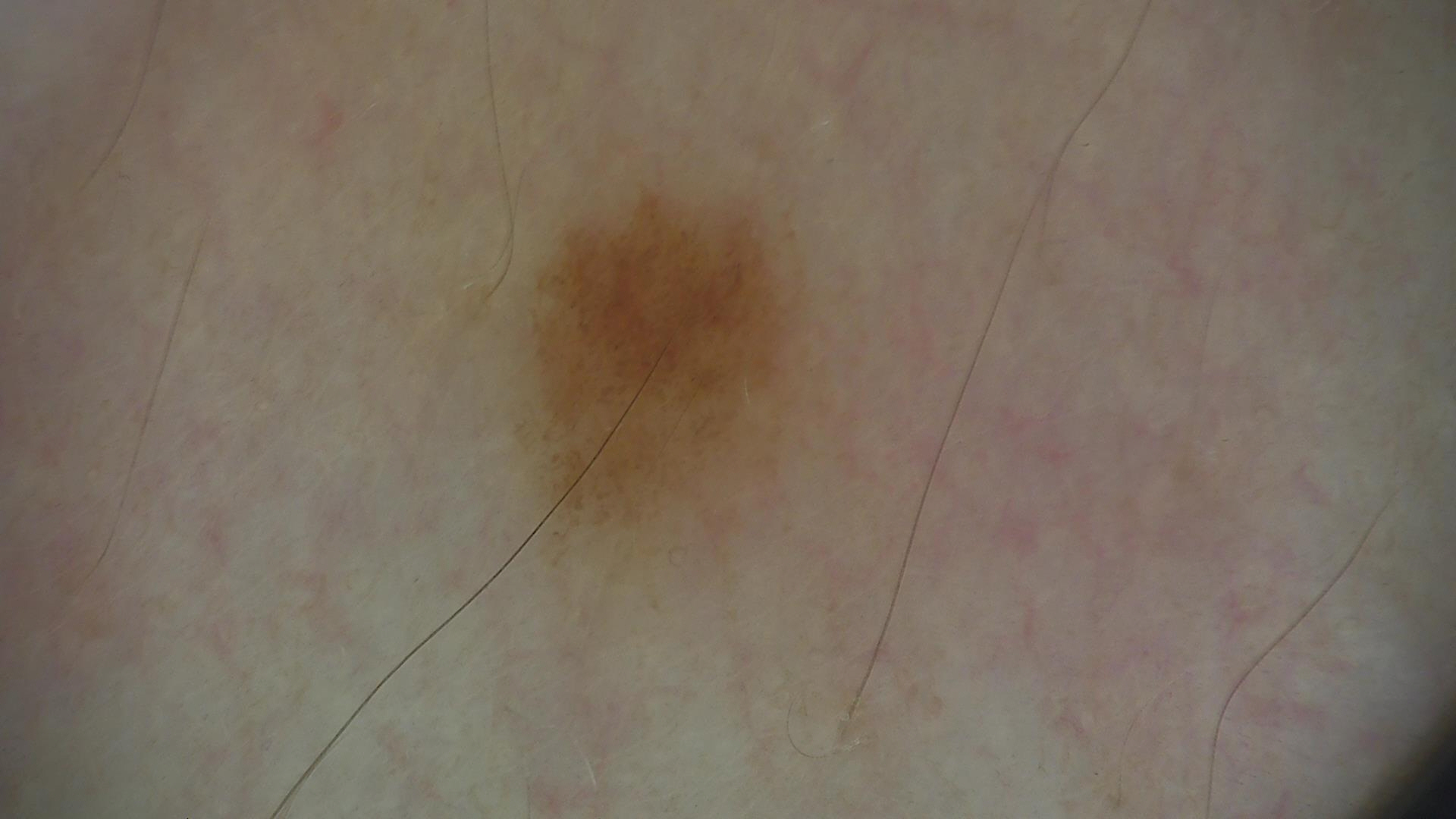Consistent with a dysplastic junctional nevus.